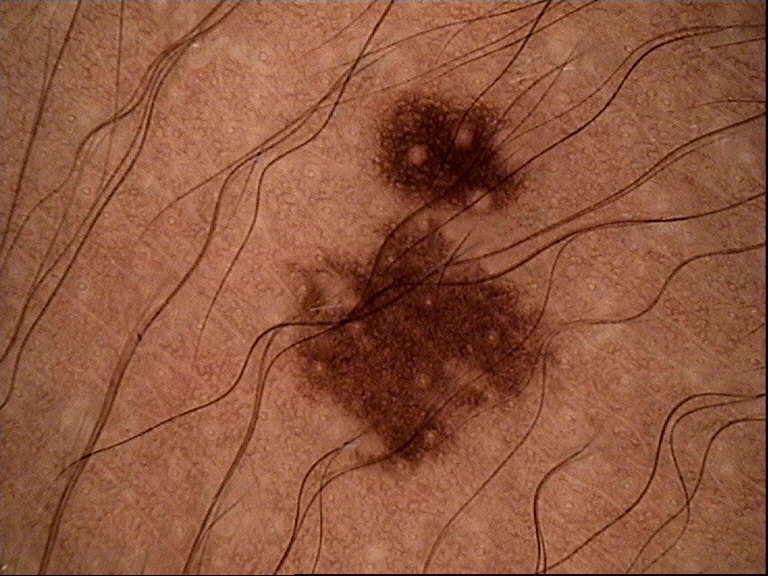Case:
* modality · dermatoscopy
* label · dysplastic junctional nevus (expert consensus)